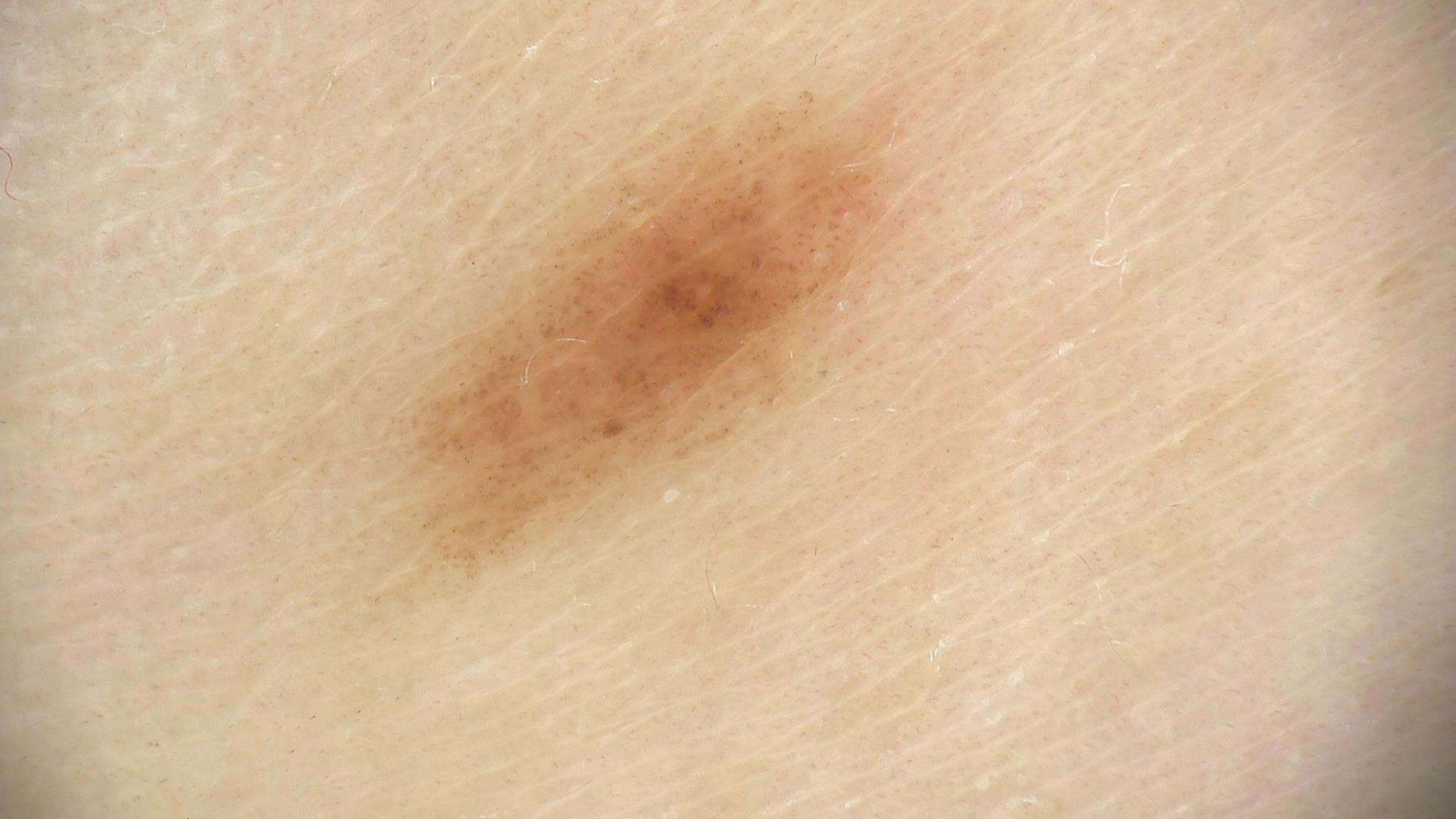Findings: A dermoscopy image of a single skin lesion. The architecture is that of a banal lesion. Impression: Consistent with a junctional nevus.